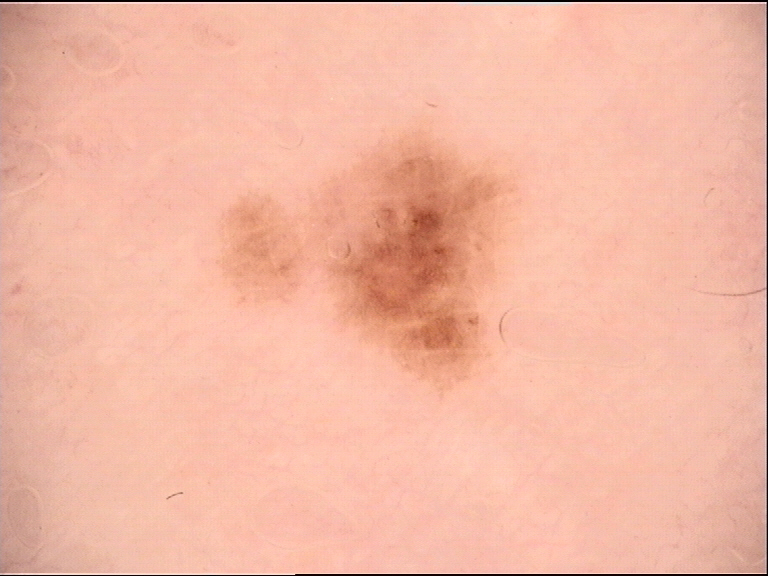Findings:
– imaging: dermoscopy
– diagnosis: dysplastic junctional nevus (expert consensus)